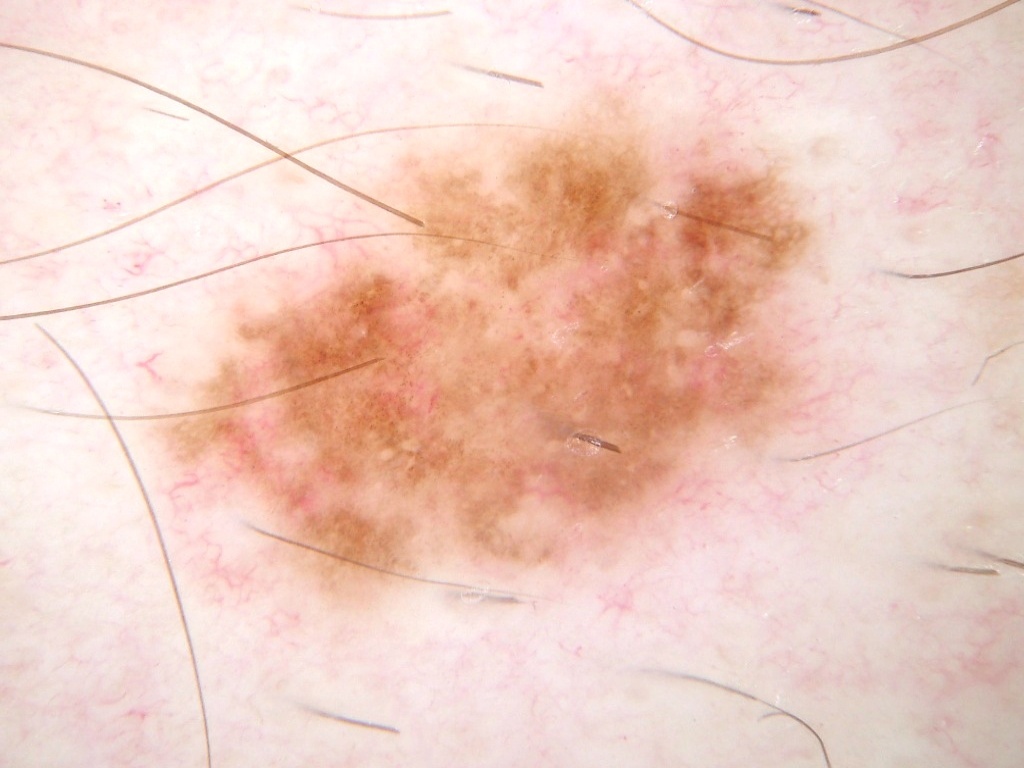Summary:
A dermoscopy image of a single skin lesion. The subject is a male aged 43-47. With coordinates (x1, y1, x2, y2), the lesion's extent is bbox=[137, 73, 854, 633]. Dermoscopic review identifies pigment network, milia-like cysts, and negative network, with no streaks or globules.
Impression:
Consistent with a melanocytic nevus.